A female patient aged 58 to 62; dermoscopy of a skin lesion.
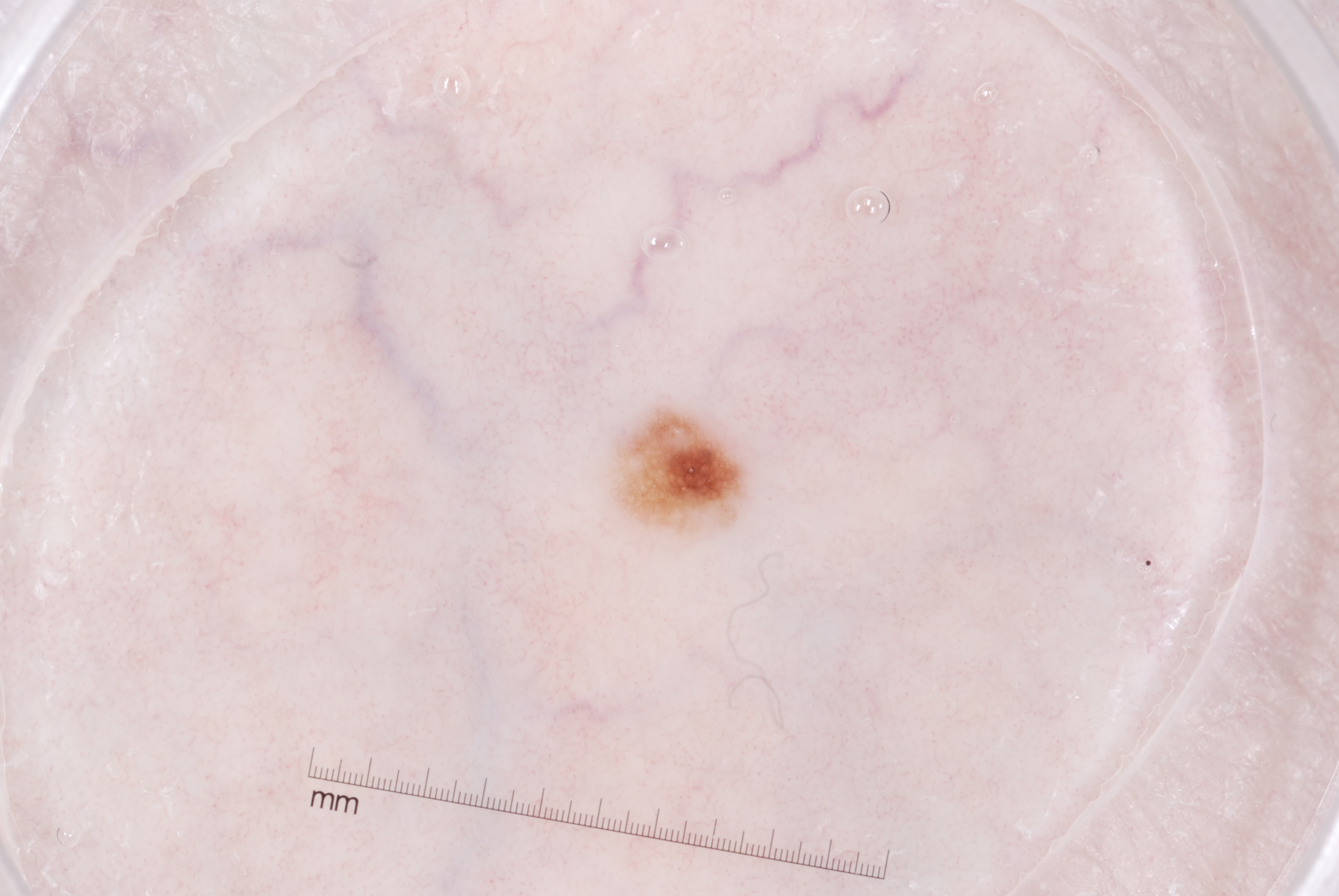Dermoscopic examination shows pigment network; no milia-like cysts, streaks, or negative network. With coordinates (x1, y1, x2, y2), lesion location: <box>607, 406, 742, 532</box>. Consistent with a melanocytic nevus.